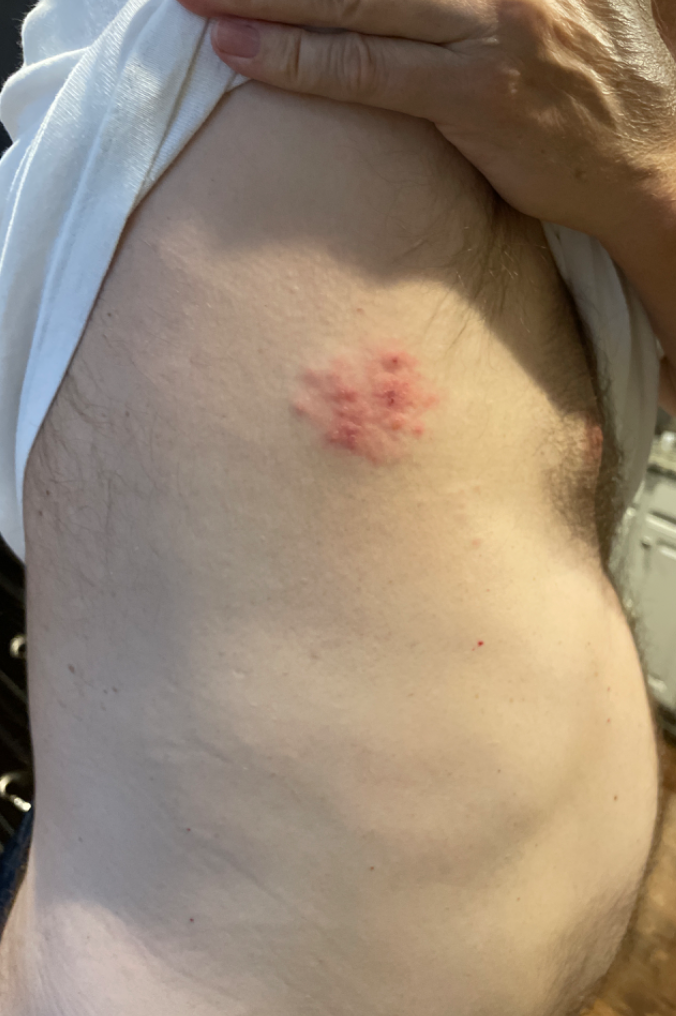Findings:
Most likely Herpes Zoster; possibly Herpes Simplex.